A close-up photograph:
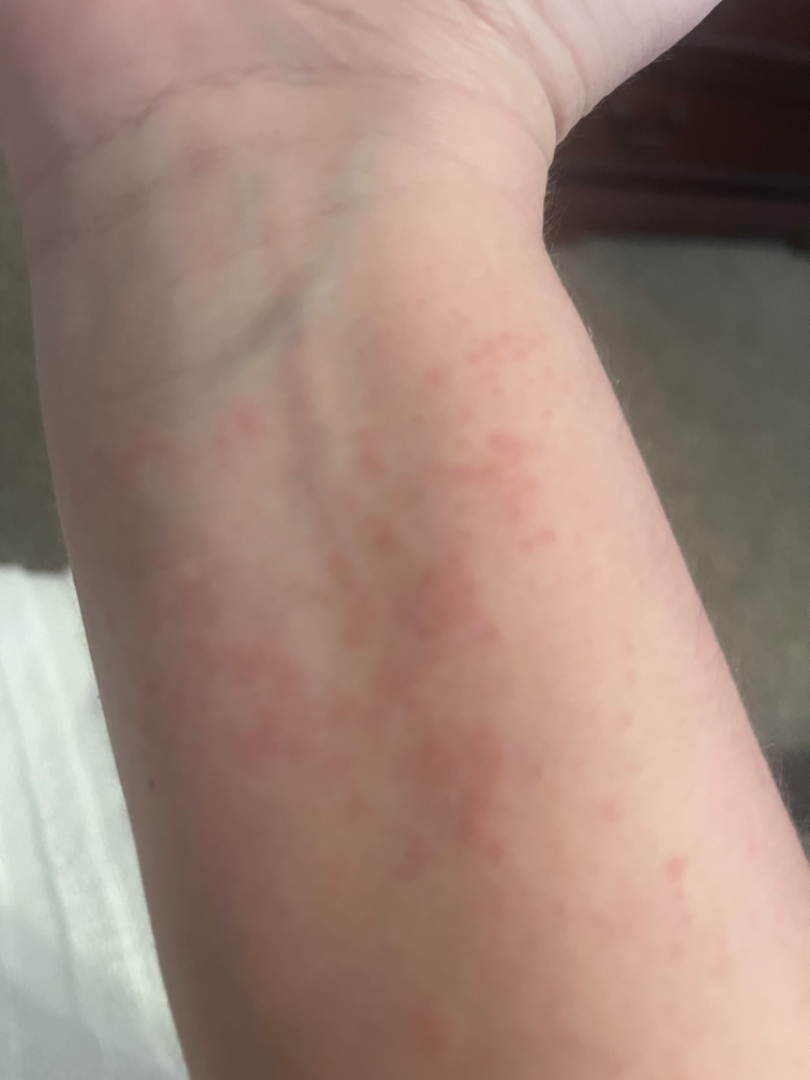The skin findings could not be characterized from the image.